A dermoscopic image of a skin lesion.
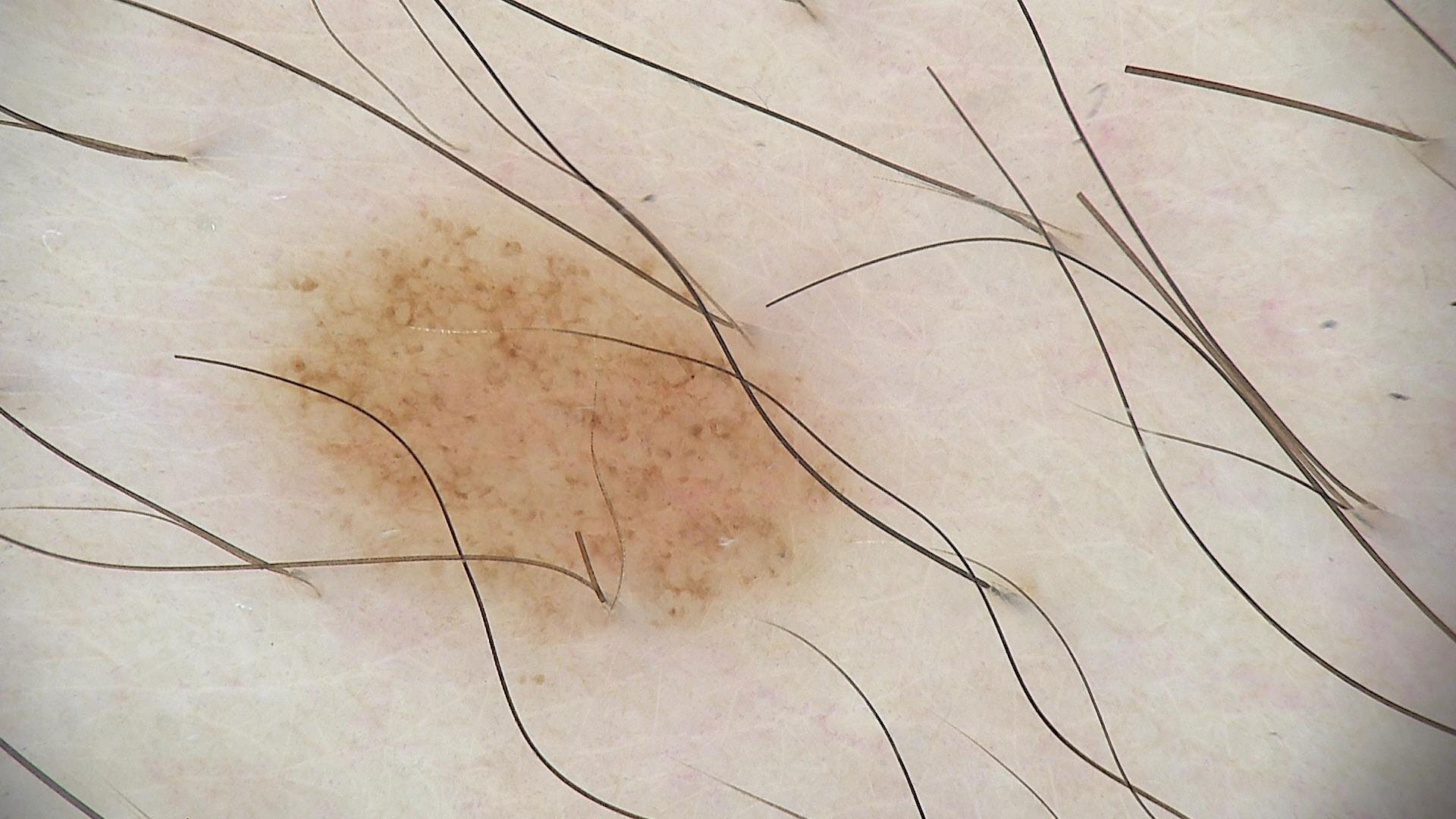label: dysplastic junctional nevus (expert consensus).